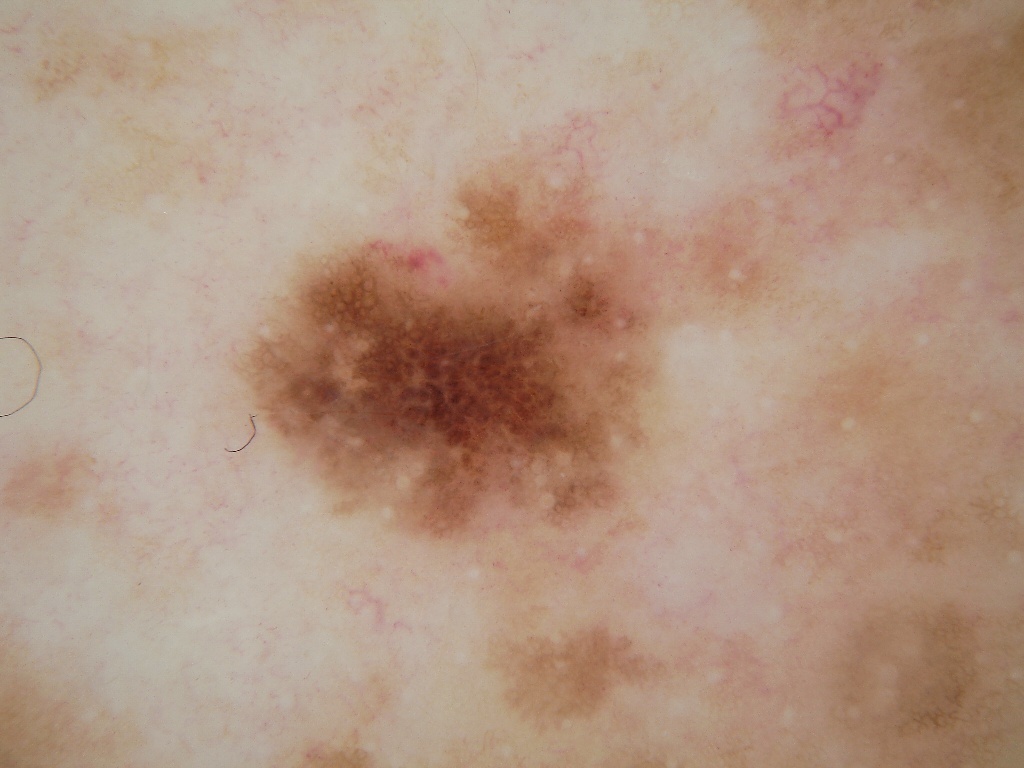Case summary: The patient is a female in their mid-60s. A skin lesion imaged with a dermatoscope. Dermoscopy demonstrates pigment network and negative network. As (left, top, right, bottom), the lesion is bounded by <bbox>245, 179, 768, 541</bbox>. Diagnosis: Histopathology confirmed a melanoma.